The patient described the issue as a rash, present for less than one week, the affected area is the arm and head or neck, texture is reported as fluid-filled, skin tone: Fitzpatrick VI; non-clinician graders estimated a Monk skin tone scale of 8, a close-up photograph — 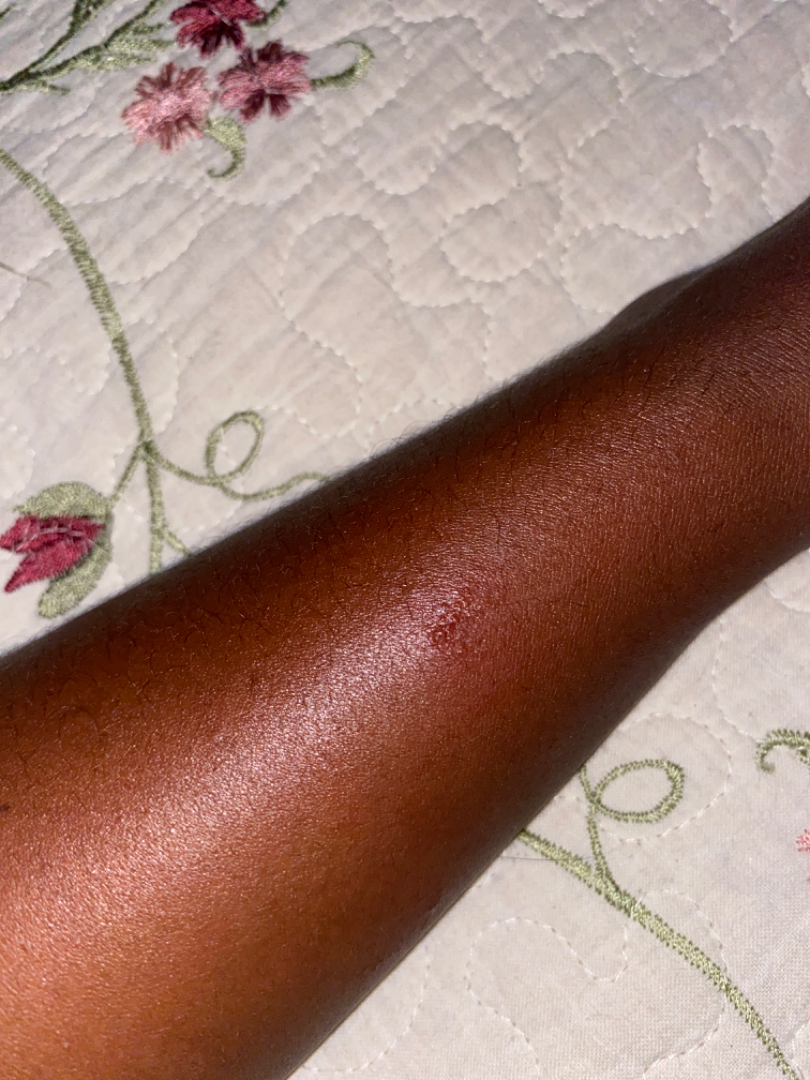Diagnostic features were not clearly distinguishable in this photograph.